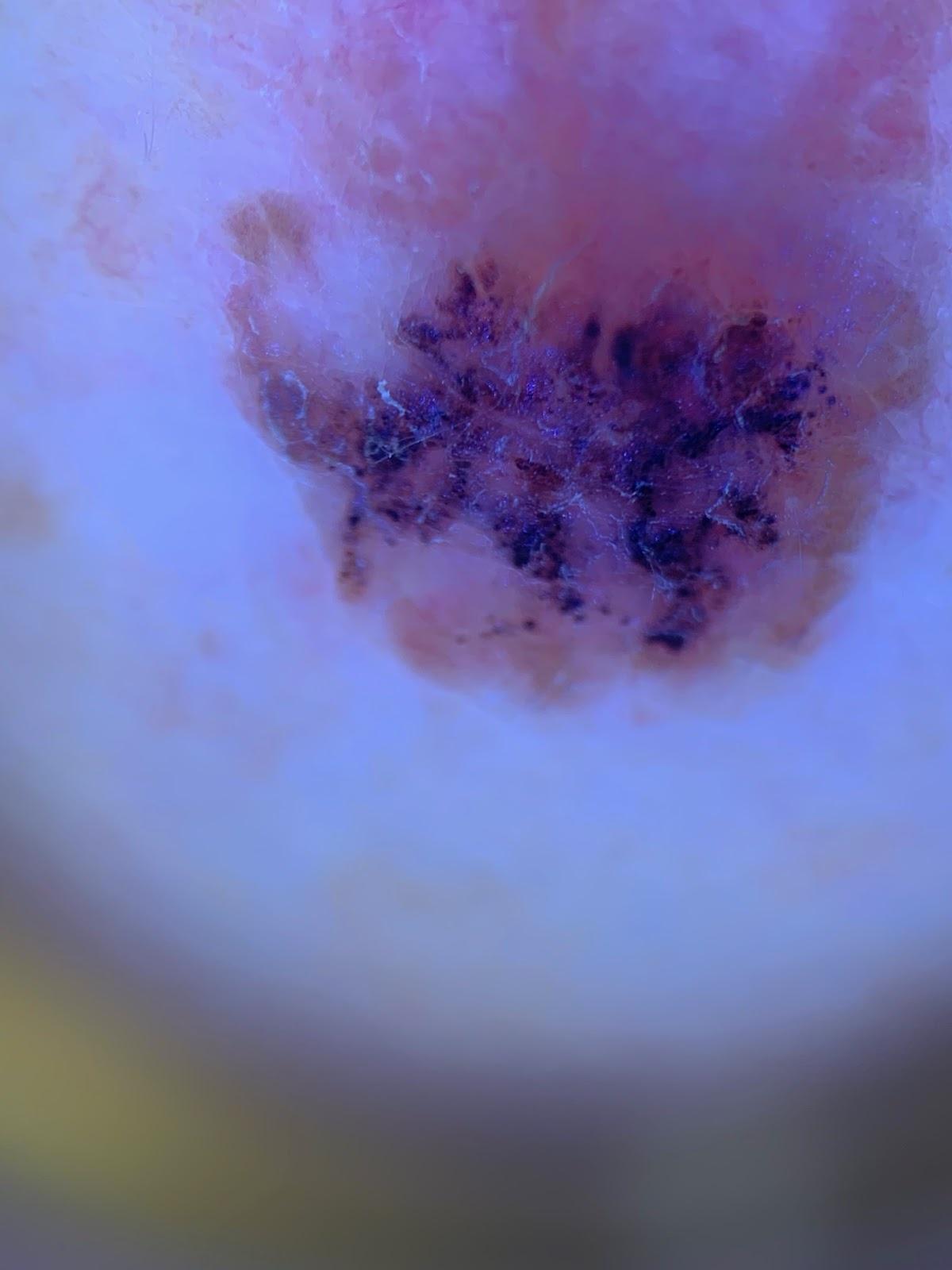diagnosis=Melanoma (biopsy-proven)